Texture is reported as flat. Self-categorized by the patient as a rash. The condition has been present for one to four weeks. The contributor is a male aged 30–39. The leg is involved. A close-up photograph. No relevant systemic symptoms — 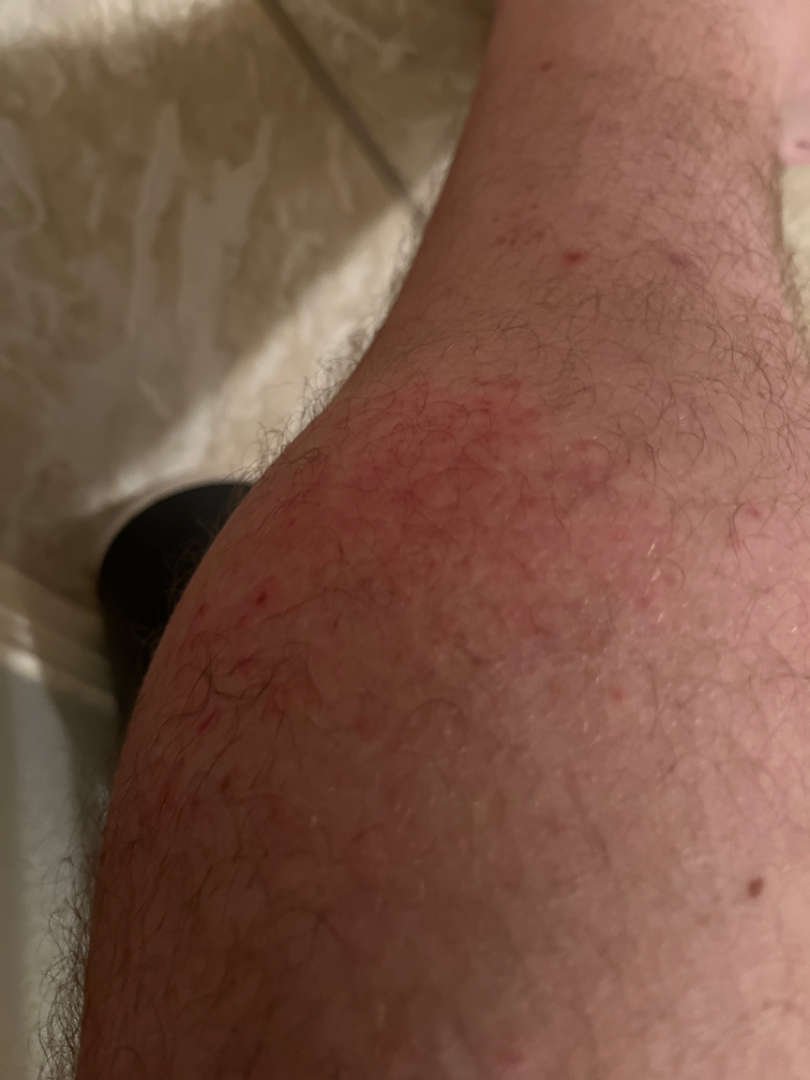Findings:
- assessment: indeterminate